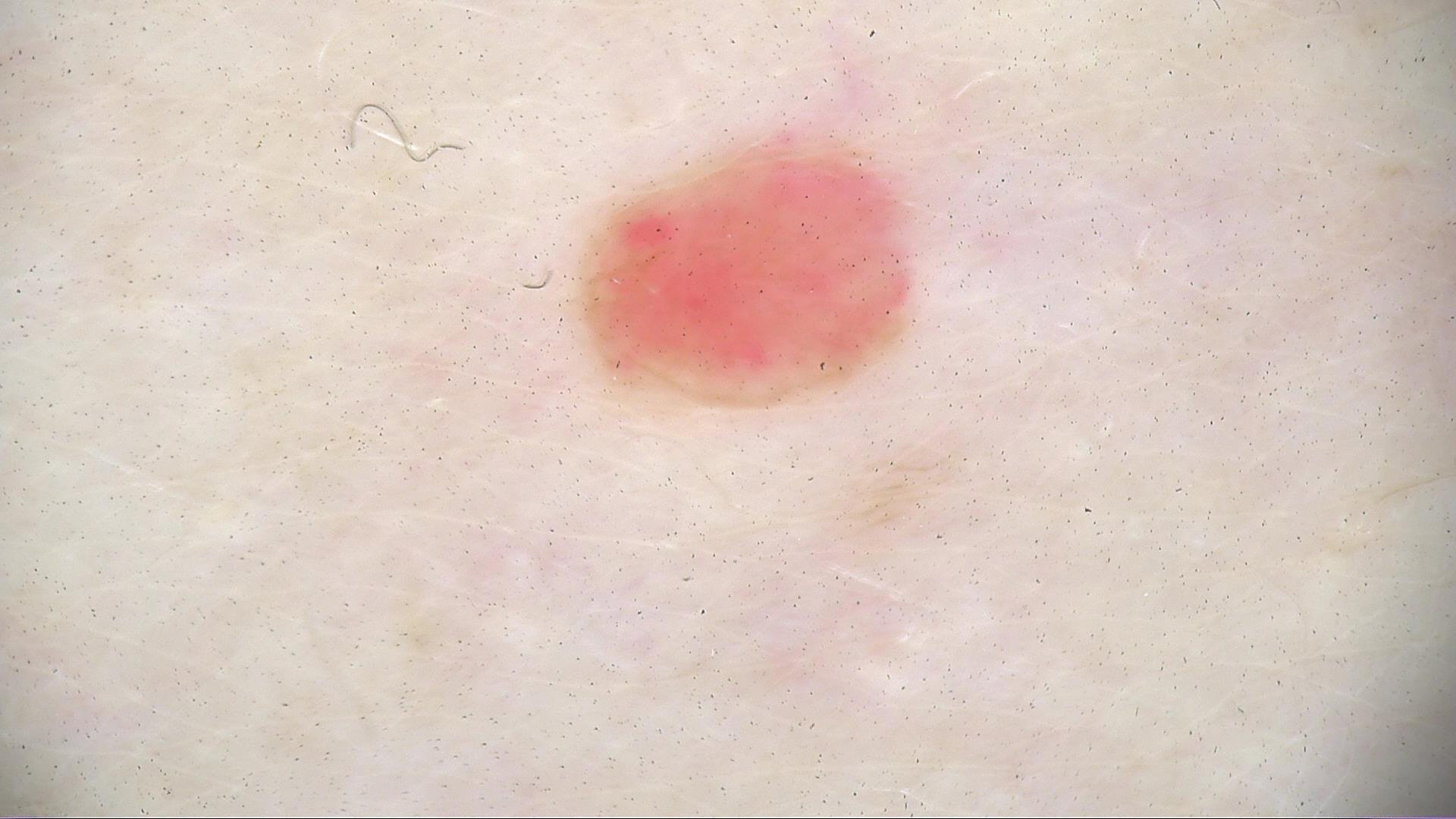<dermoscopy>
<image>dermatoscopy</image>
<lesion_type>
<main_class>vascular</main_class>
</lesion_type>
<diagnosis>
<name>hemangioma</name>
<code>ha</code>
<malignancy>benign</malignancy>
<super_class>non-melanocytic</super_class>
<confirmation>expert consensus</confirmation>
</diagnosis>
</dermoscopy>